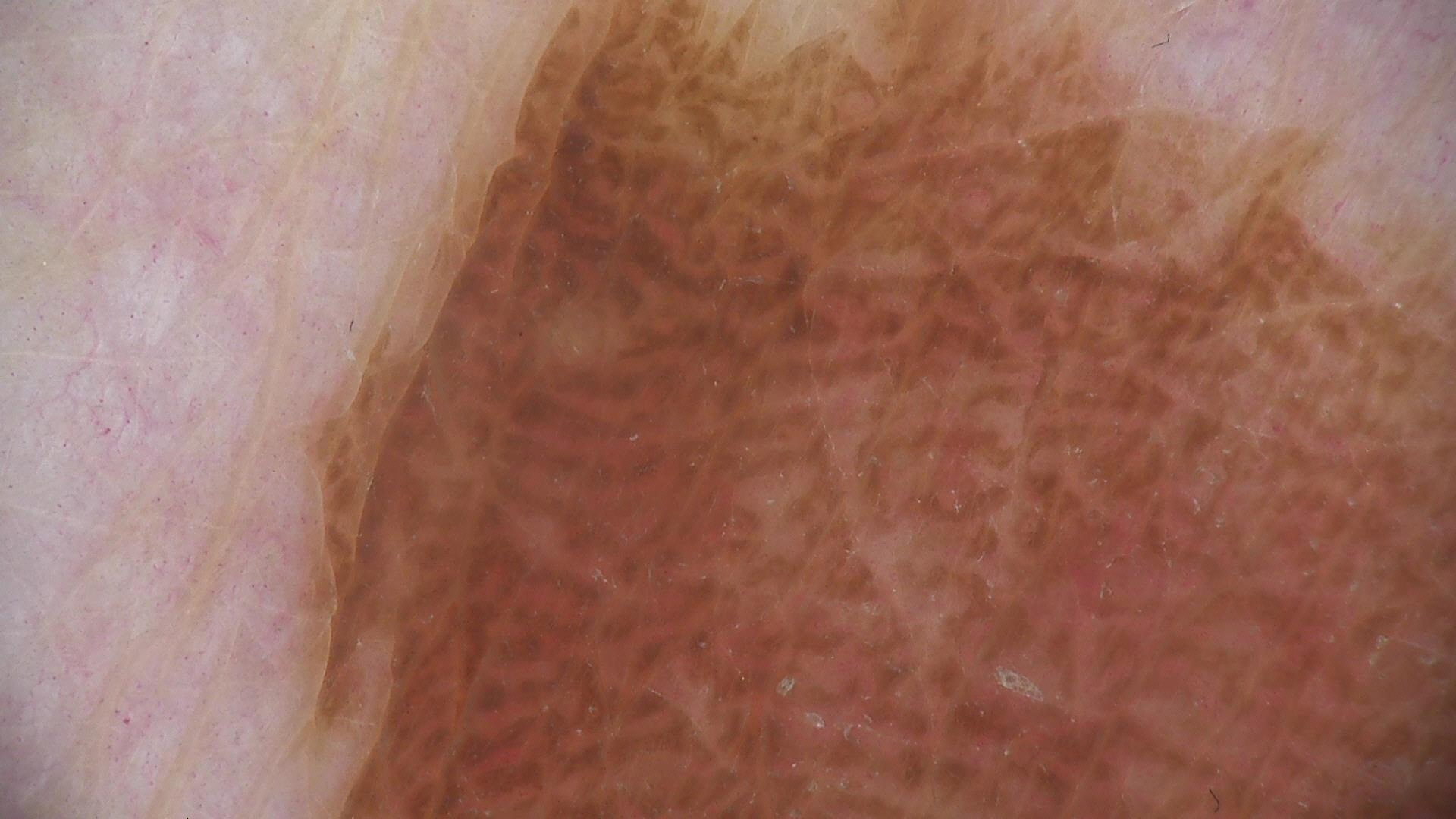Conclusion: Diagnosed as a seborrheic keratosis.